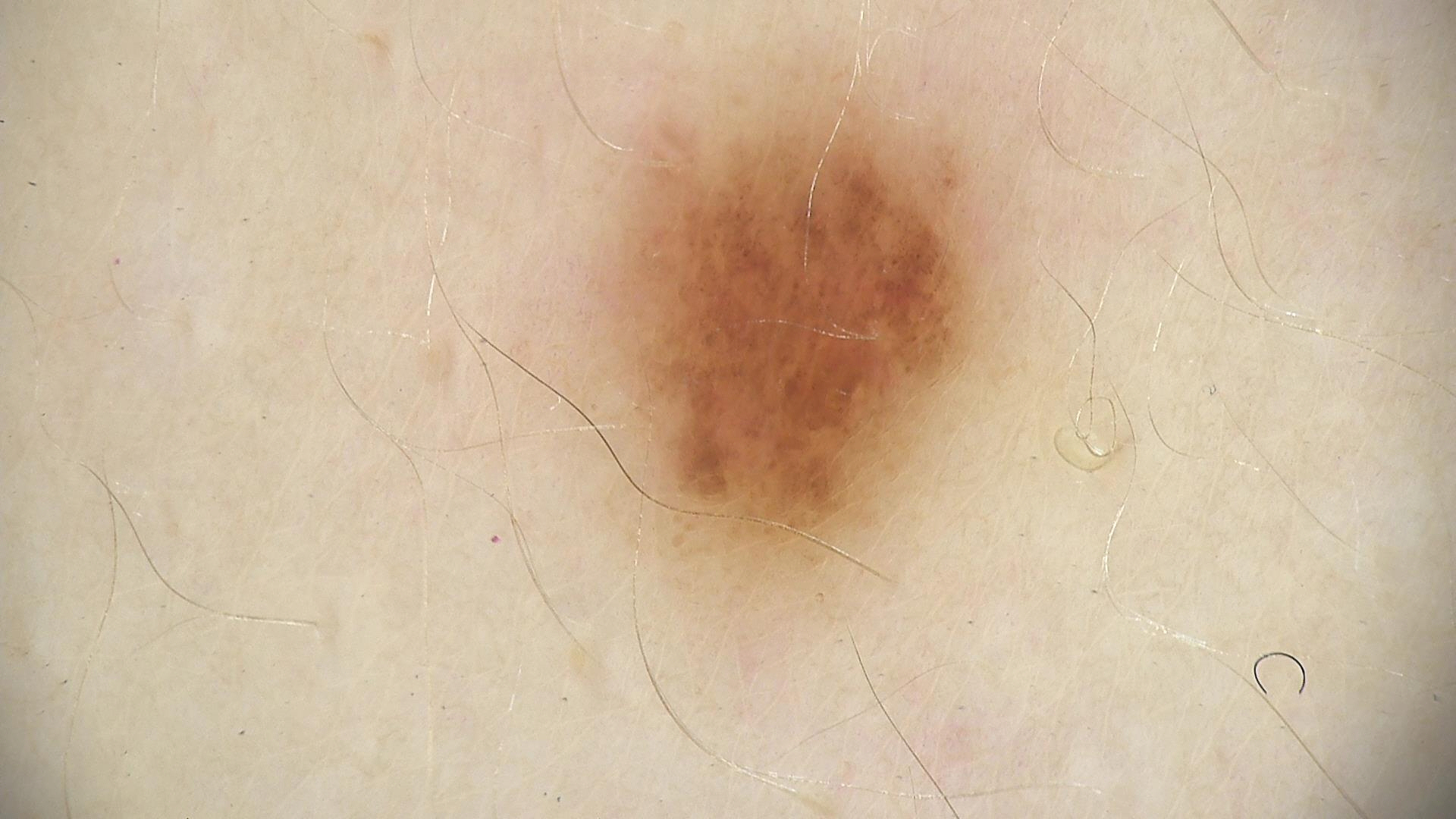Case:
– class · dysplastic junctional nevus (expert consensus)